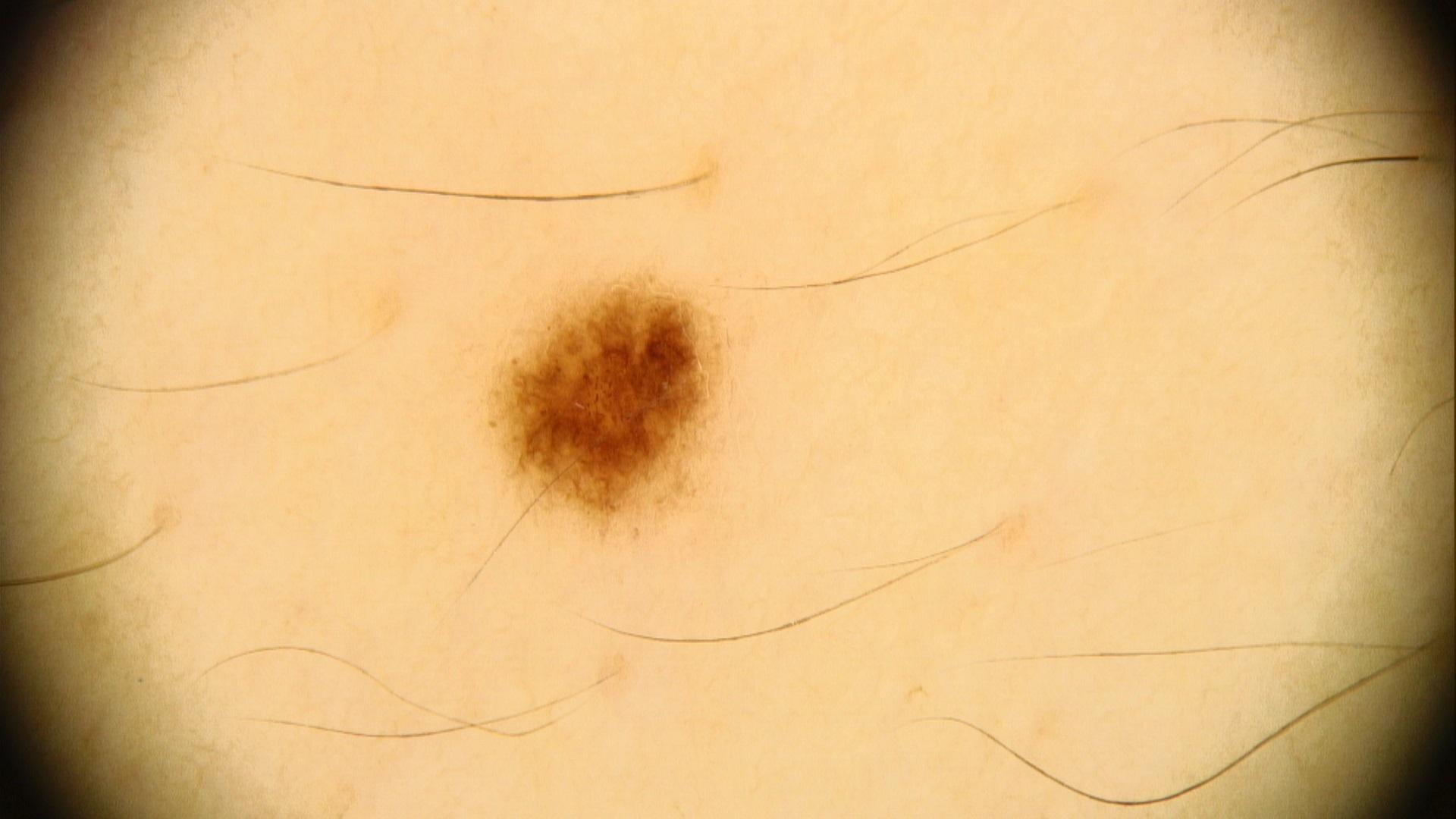risk factors: no melanoma in first-degree relatives and no prior melanoma
image type: contact-polarized dermoscopy
FST: III
anatomic site: the trunk (the anterior trunk)
impression: Nevus